The patient is male · the photograph was taken at a distance: 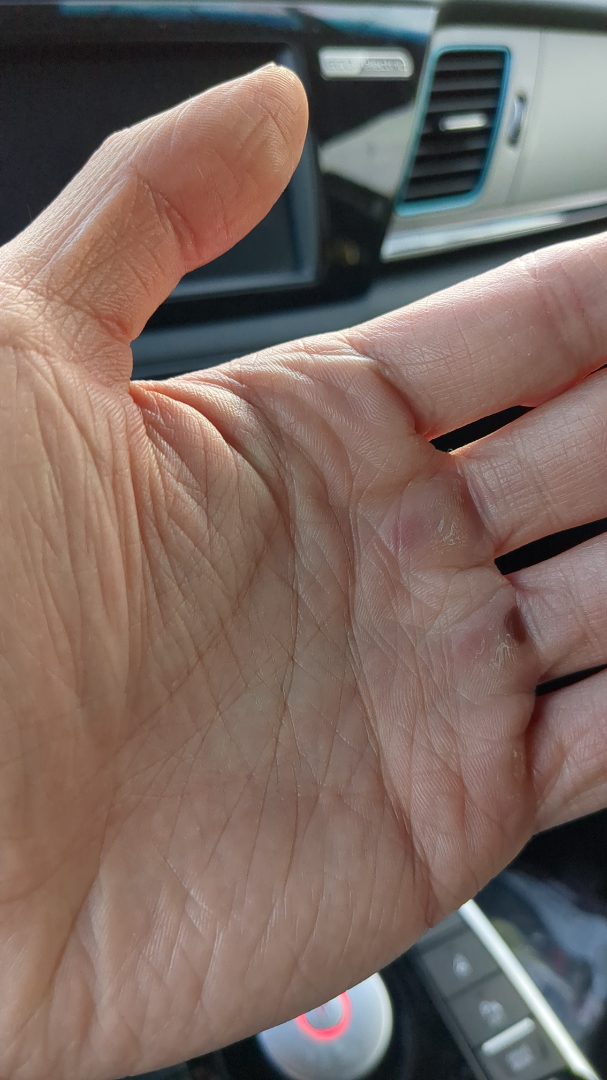The condition could not be reliably identified from the image.